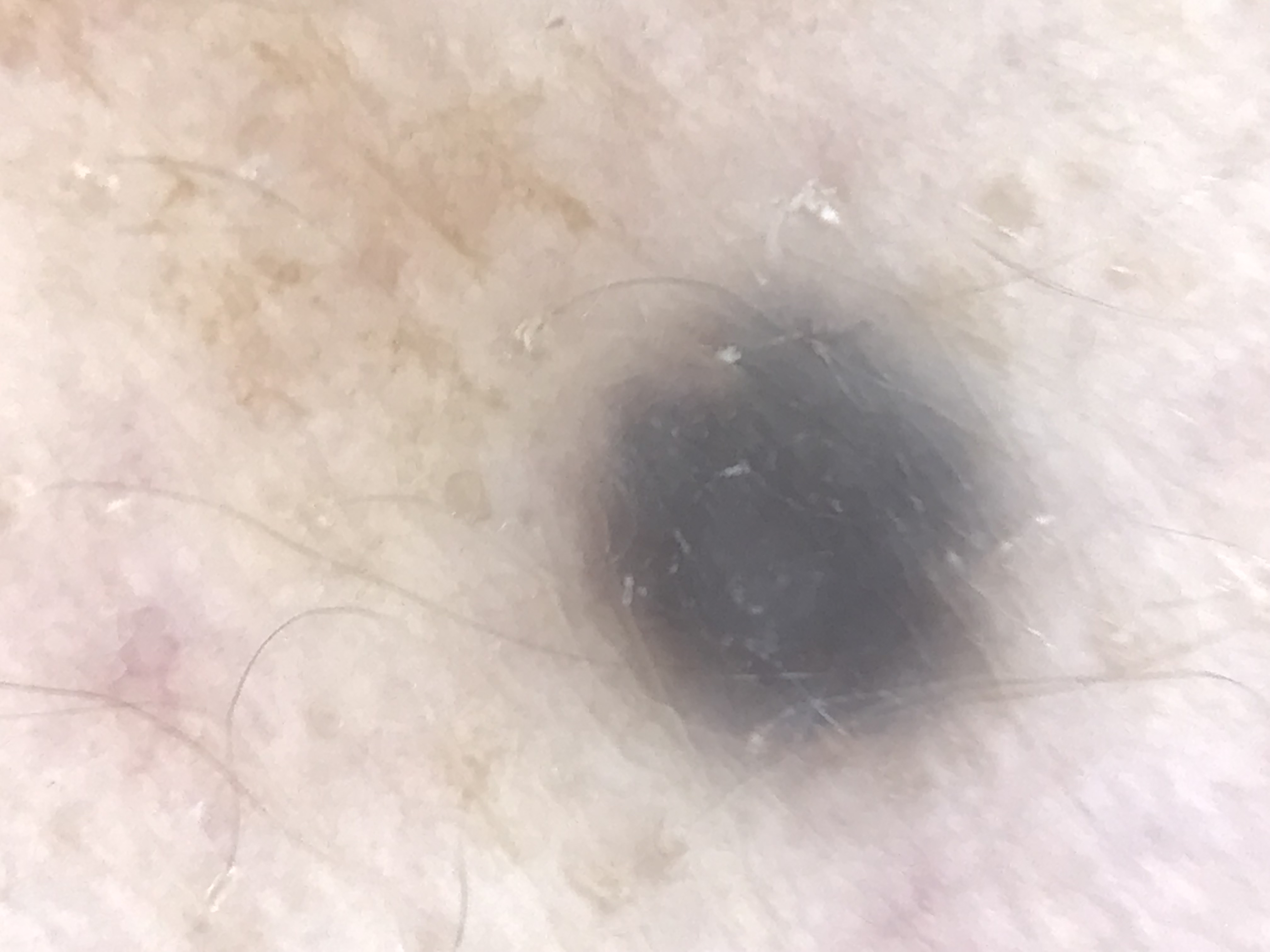A dermoscopy image of a single skin lesion. The morphology is that of a banal, dermal lesion. Classified as a blue nevus.